The photograph is a close-up of the affected area.
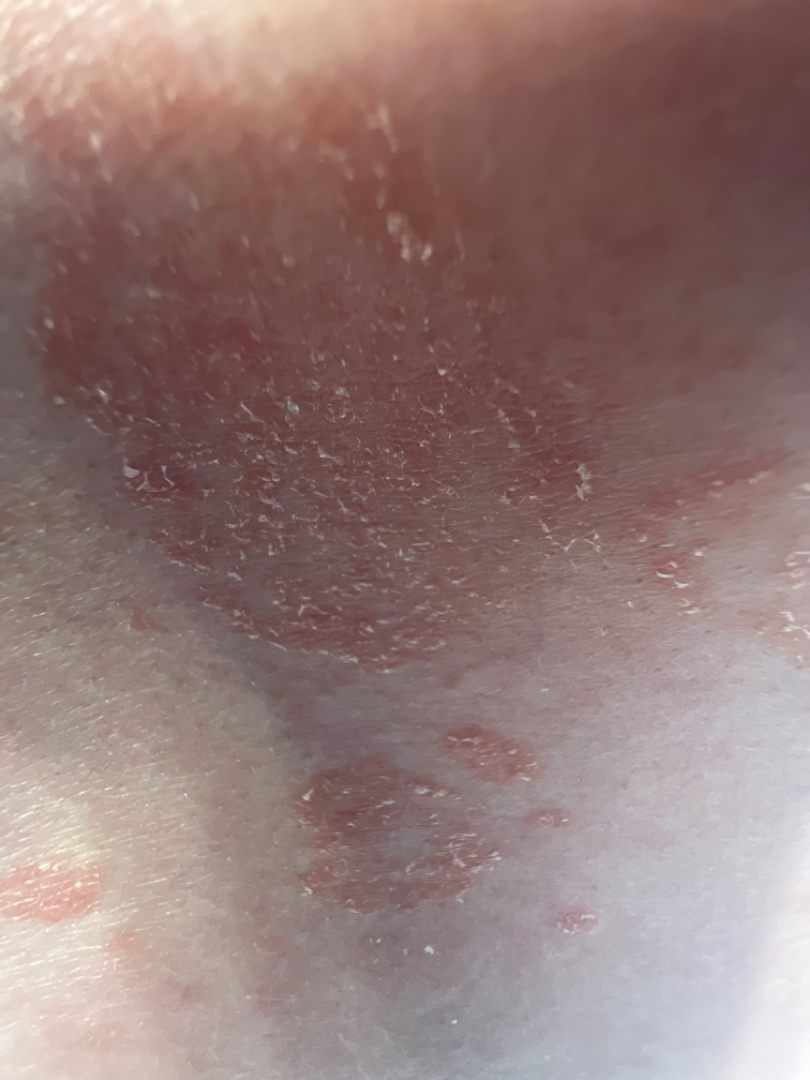The condition could not be reliably identified from the image.